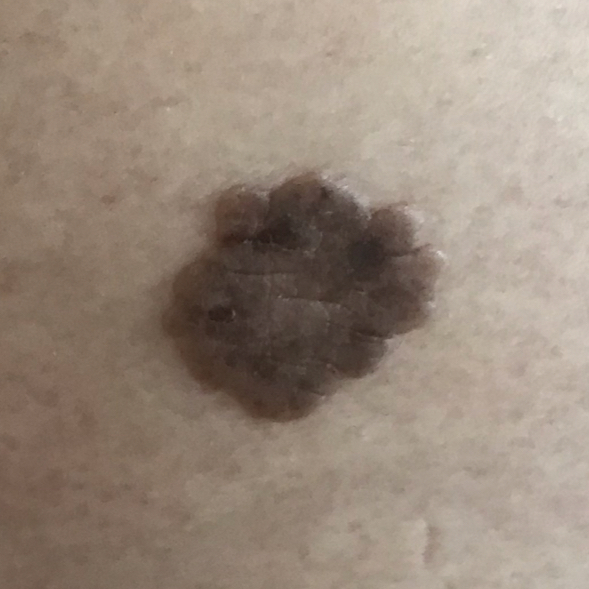A clinical close-up photograph of a skin lesion. By the patient's account, the lesion is elevated. Consistent with a benign skin lesion — a seborrheic keratosis.